A dermoscopic photograph of a skin lesion:
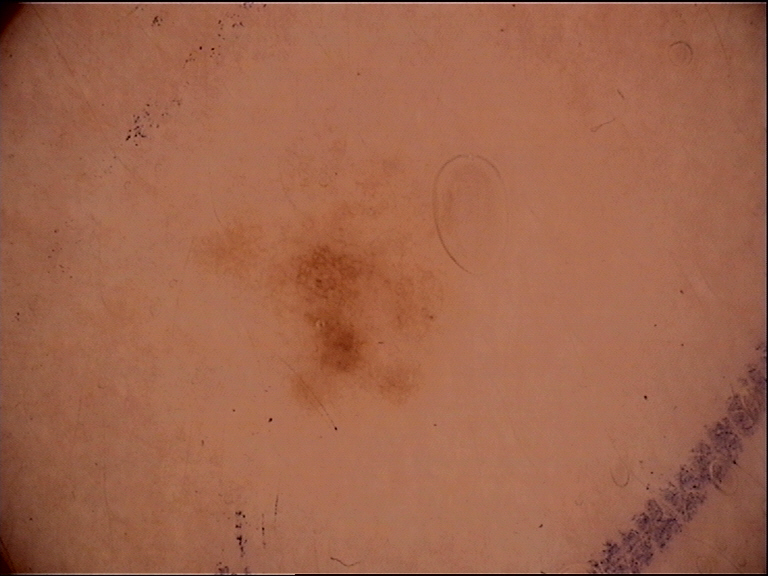diagnosis: dysplastic junctional nevus (expert consensus).